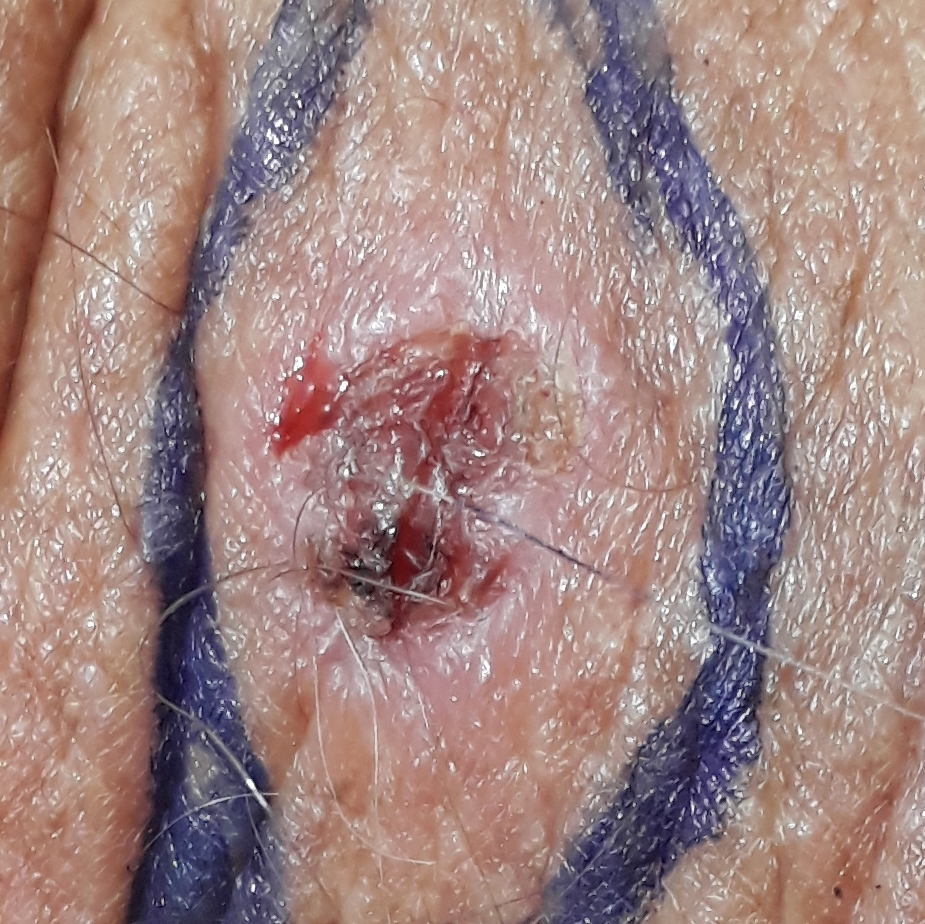| feature | finding |
|---|---|
| modality | clinical photograph |
| region | the neck |
| symptoms | pain, growth, bleeding, elevation, itching |
| diagnostic label | basal cell carcinoma (biopsy-proven) |